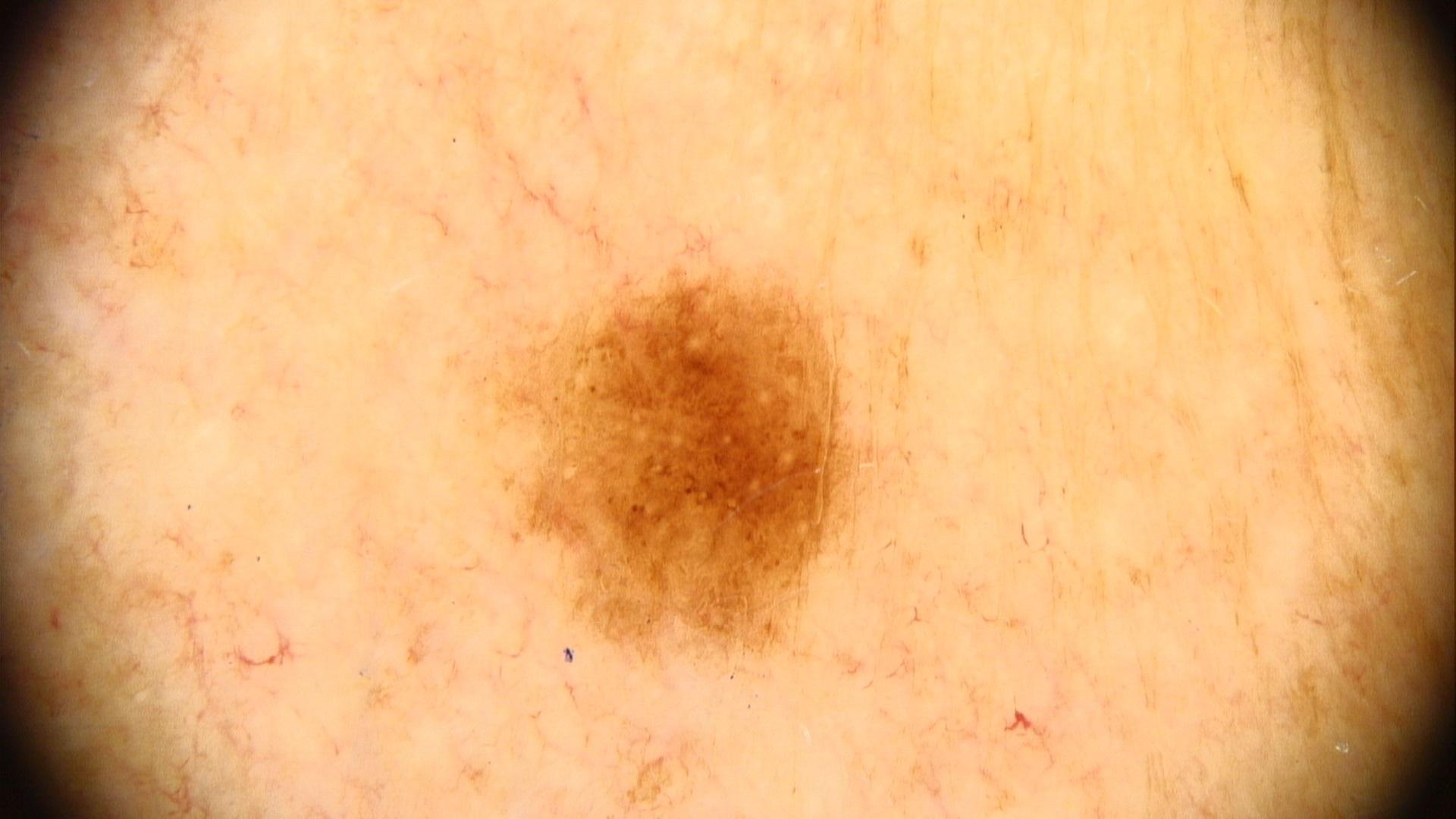{
  "image": "dermoscopic image",
  "patient": {
    "age_approx": 40,
    "sex": "male"
  },
  "diagnosis": {
    "name": "Nevus",
    "malignancy": "benign",
    "confirmation": "expert clinical impression",
    "lineage": "melanocytic"
  }
}